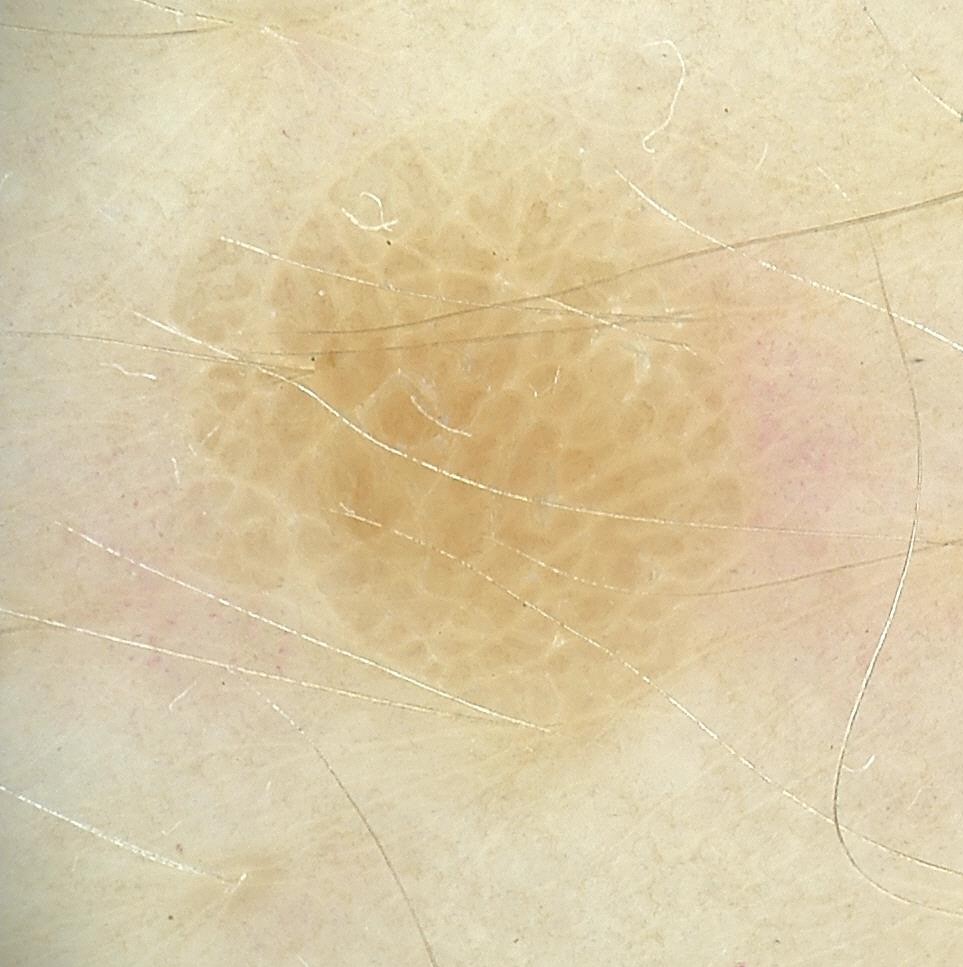Labeled as a seborrheic keratosis.